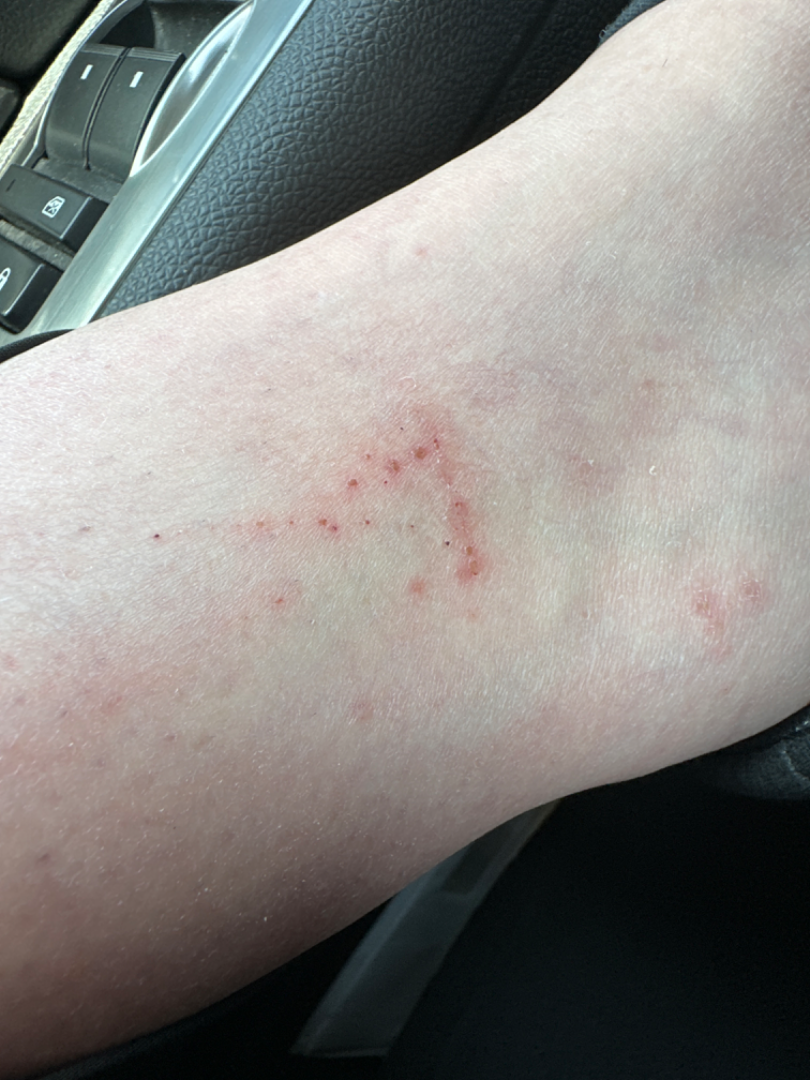The case was indeterminate on photographic review. Close-up view.